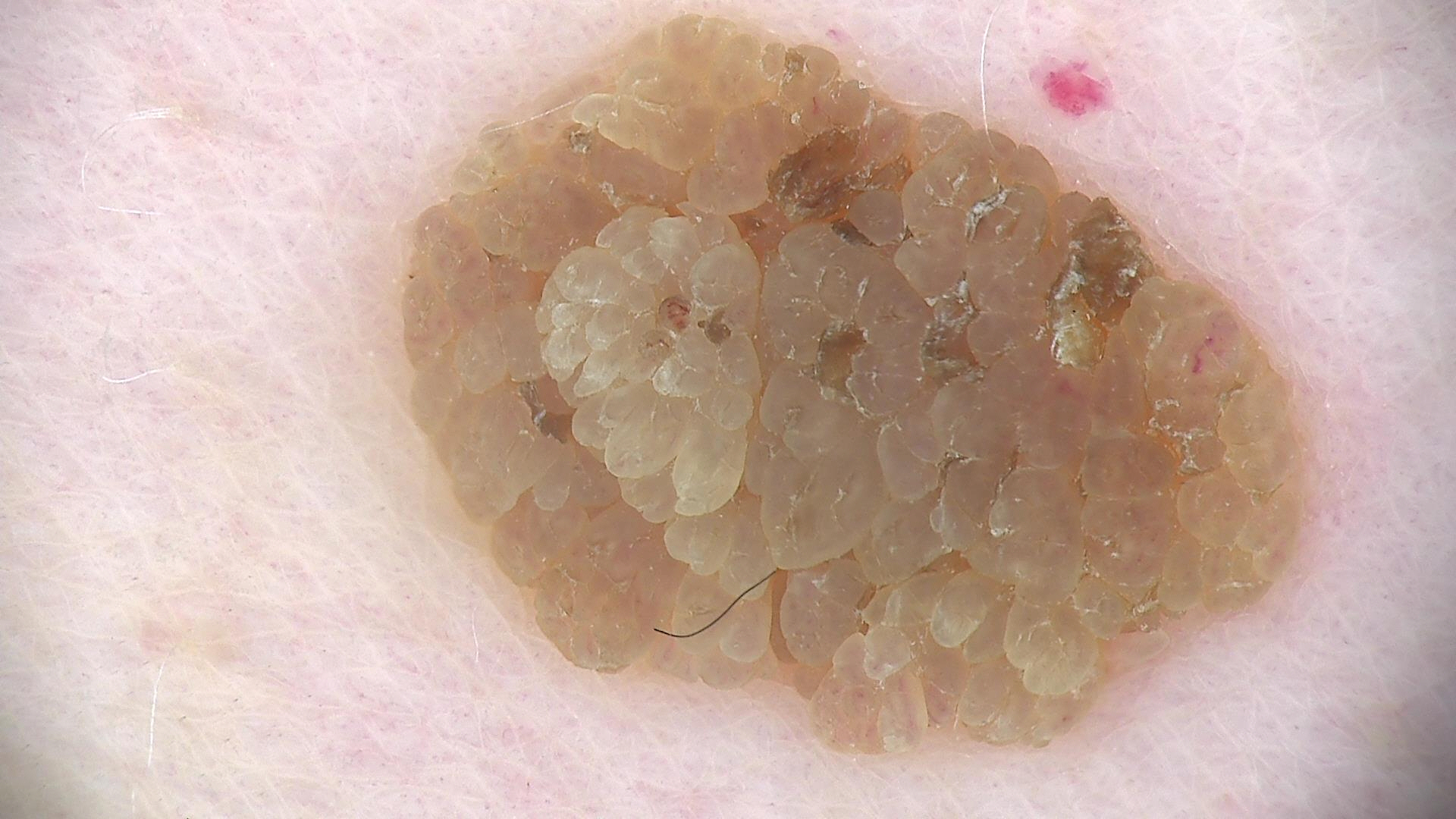Findings: This is a keratinocytic lesion. Conclusion: The diagnostic label was a seborrheic keratosis.